A skin lesion imaged with a dermatoscope.
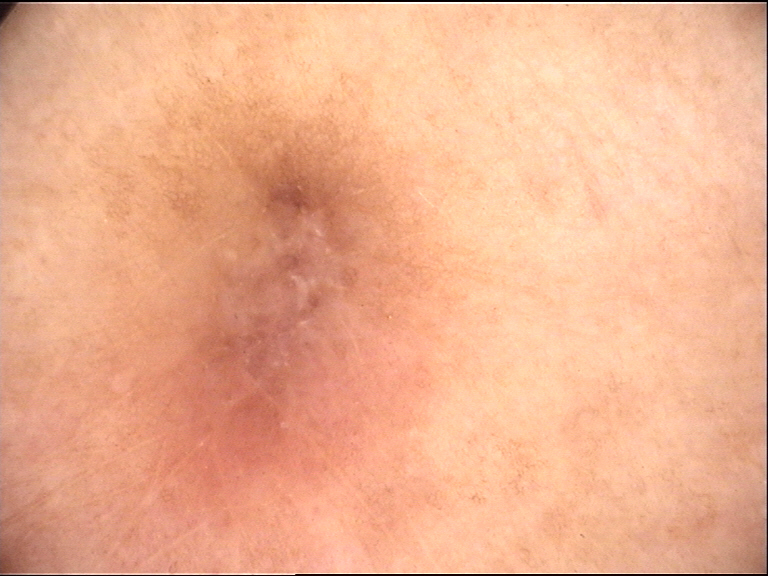  lesion_type:
    main_class: fibro-histiocytic
  diagnosis:
    name: dermatofibroma
    code: df
    malignancy: benign
    super_class: non-melanocytic
    confirmation: expert consensus